The arm is involved; female subject, age 40–49; close-up view.
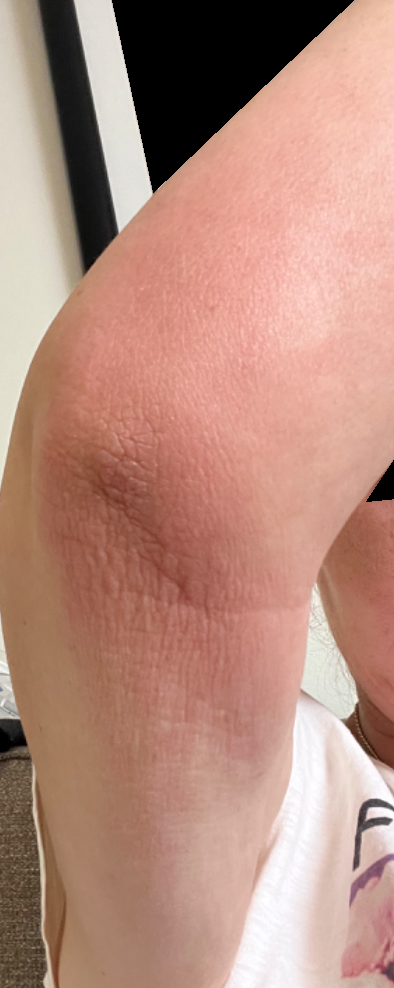Impression: Allergic Contact Dermatitis (weight 0.50); Irritant Contact Dermatitis (weight 0.50).